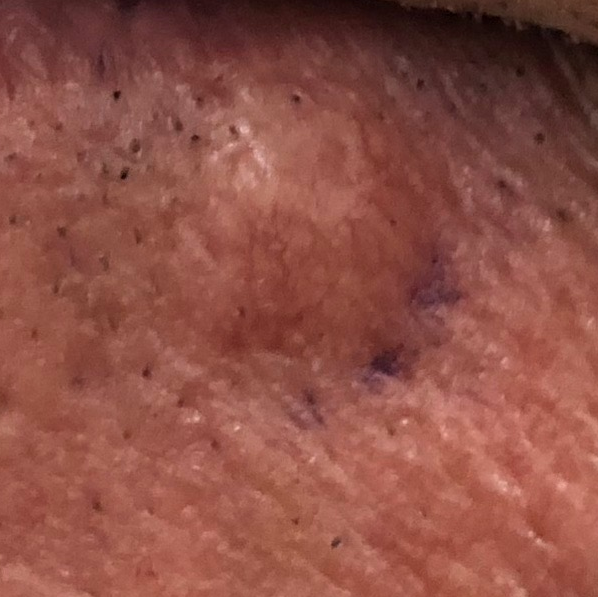By history, prior skin cancer (patient or family), prior malignancy (patient or family), and alcohol use. A smartphone photograph of a skin lesion. The patient is Fitzpatrick skin type II. A male patient aged 51. The lesion is on a lip. Measuring about 8 × 7 mm. By the patient's account, the lesion is elevated, but does not hurt and does not itch. On biopsy, the diagnosis was a basal cell carcinoma.